Reported lesion symptoms include darkening and burning, the patient reports the condition has been present for one to three months, the patient reports associated mouth sores, this is a close-up image:
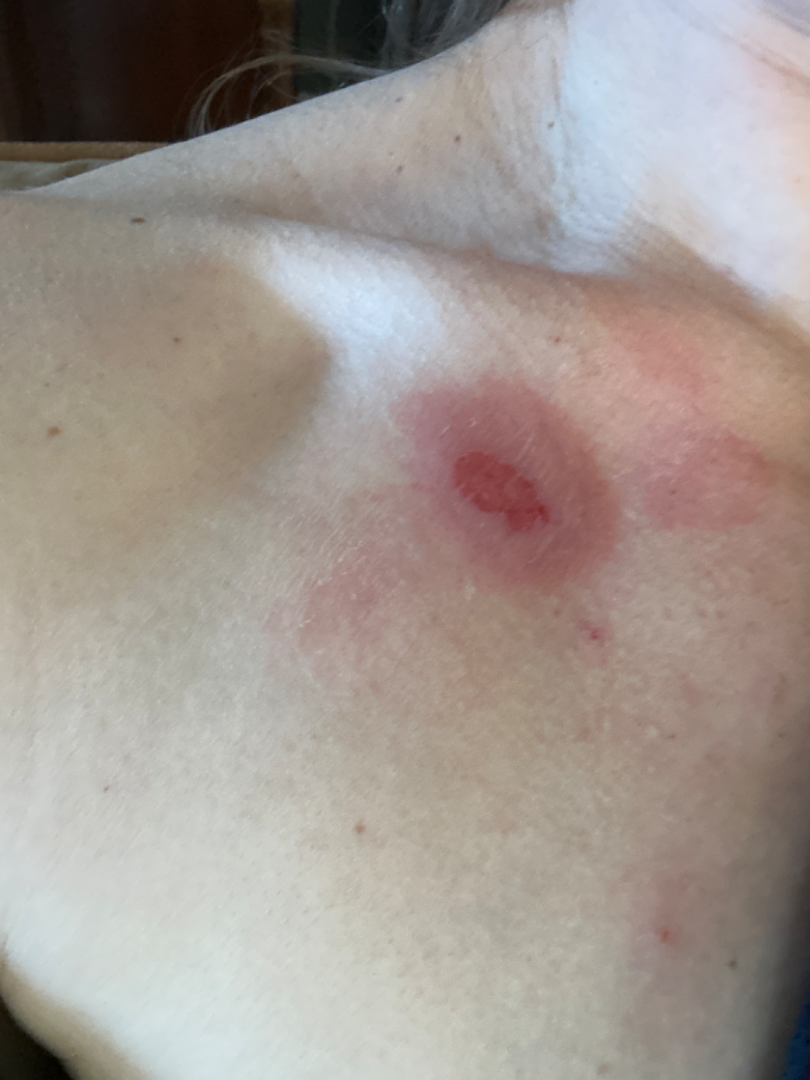clinical impression: the favored diagnosis is Insect Bite; the differential also includes Blister.